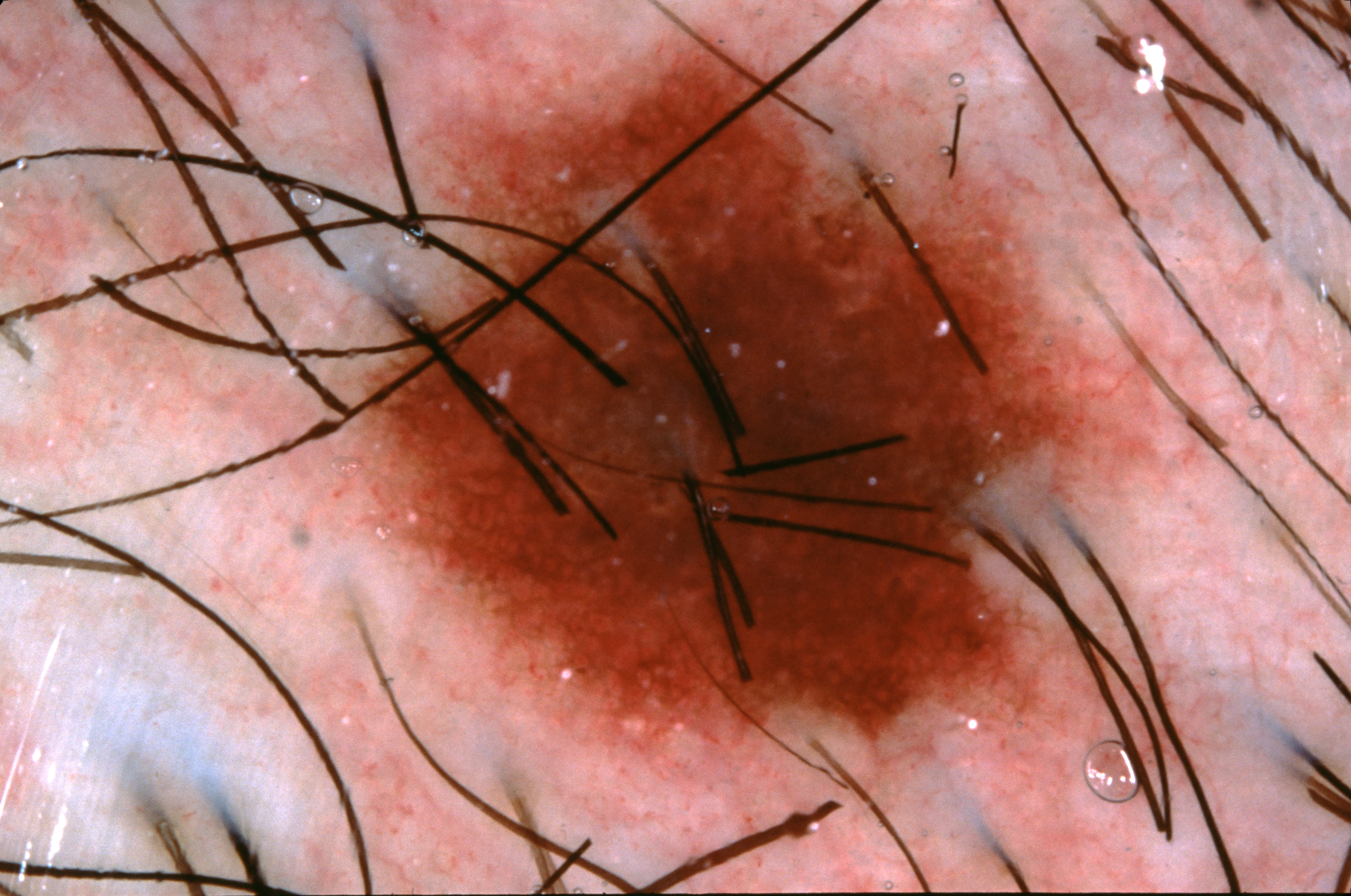A dermoscopic close-up of a skin lesion. In (x1, y1, x2, y2) order, the lesion is bounded by <box>315, 18, 1270, 808</box>. The diagnostic assessment was a melanocytic nevus.